A dermoscopic photograph of a skin lesion.
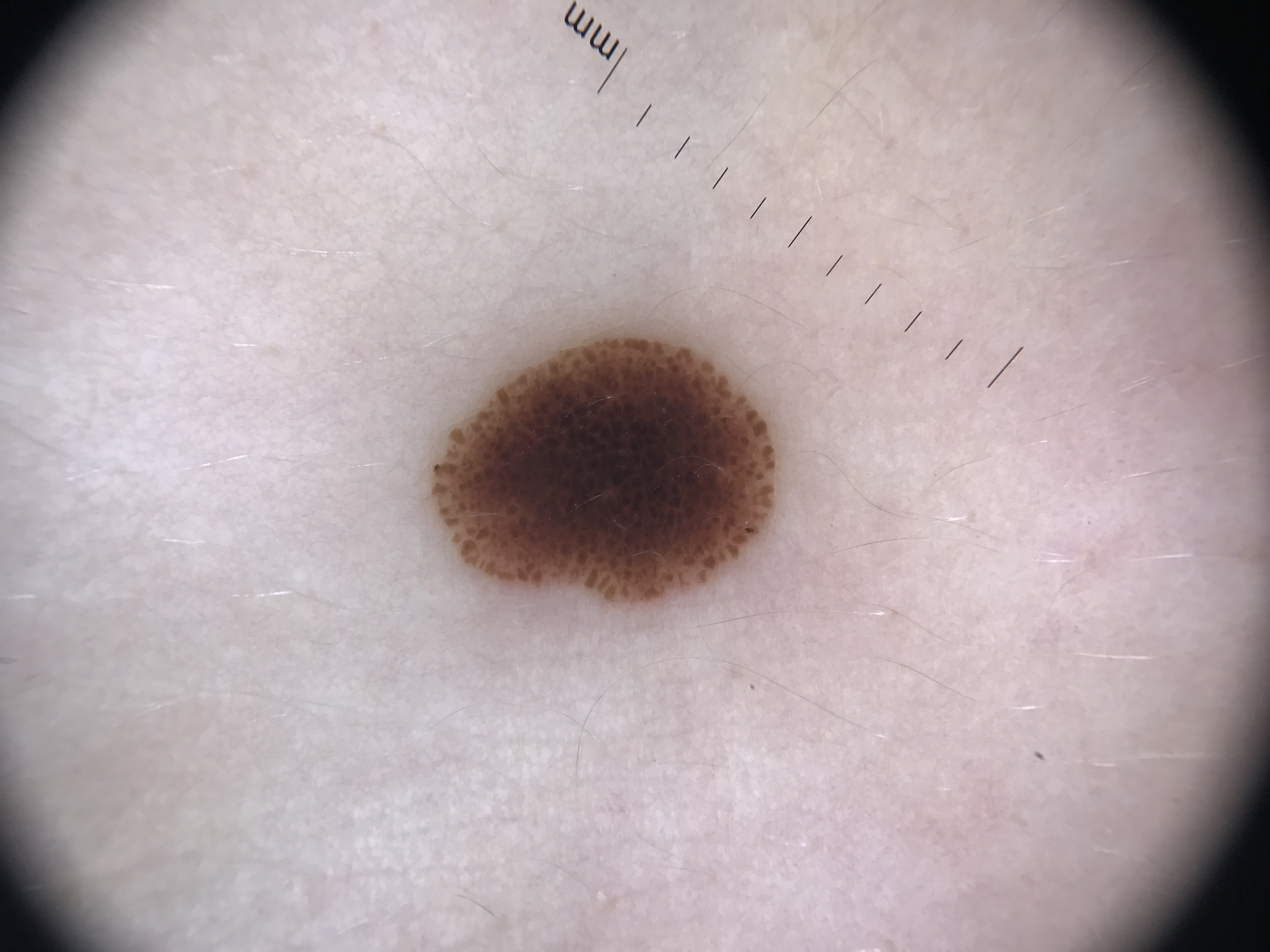classification = banal
assessment = junctional nevus (expert consensus)